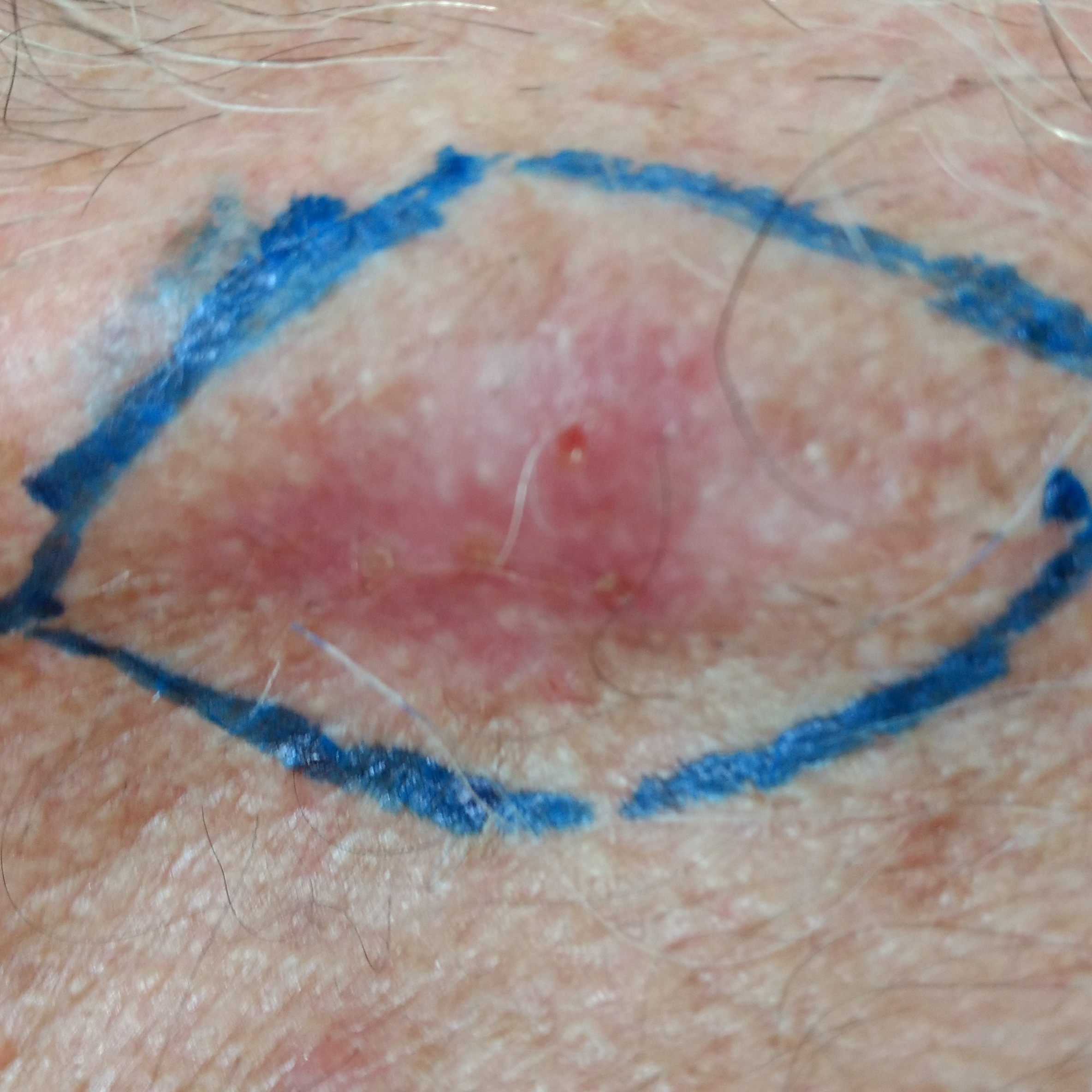Histopathology confirmed a basal cell carcinoma.